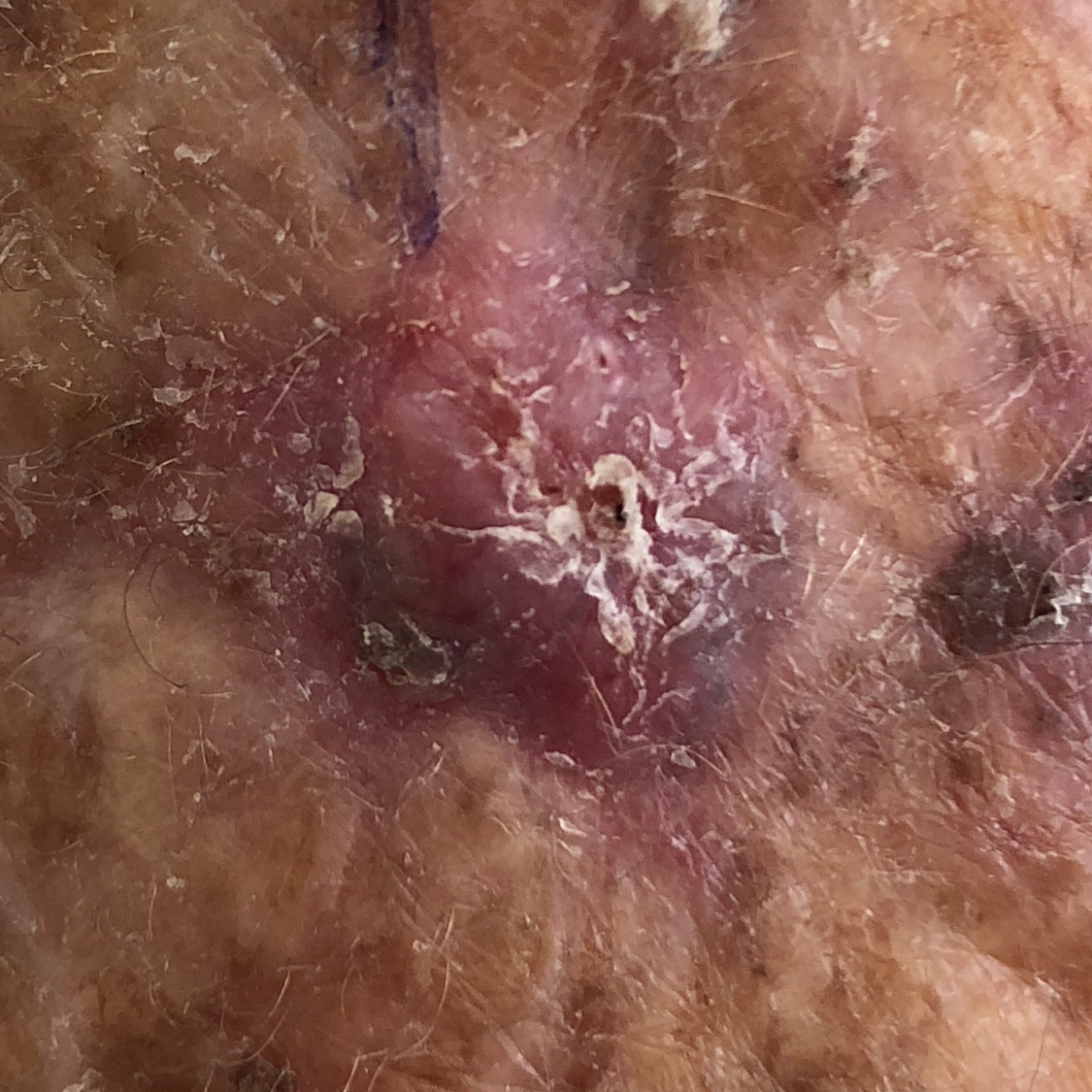image type = clinical photo; patient-reported symptoms = itching, growth, elevation, pain; pathology = basal cell carcinoma (biopsy-proven).